Dermoscopy of a skin lesion:
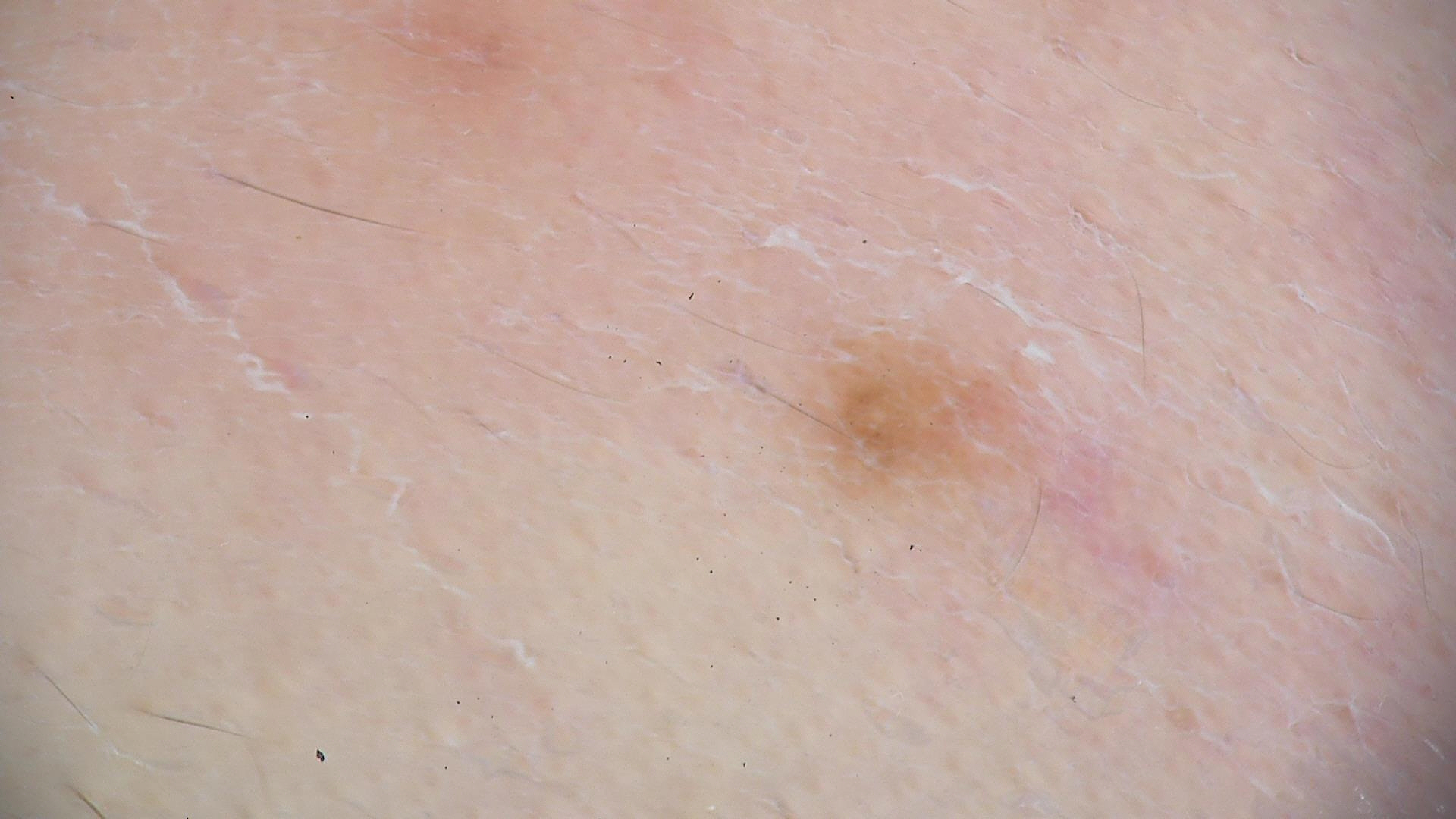The architecture is that of a banal lesion. The diagnostic label was a junctional nevus.